A dermoscopic photograph of a skin lesion.
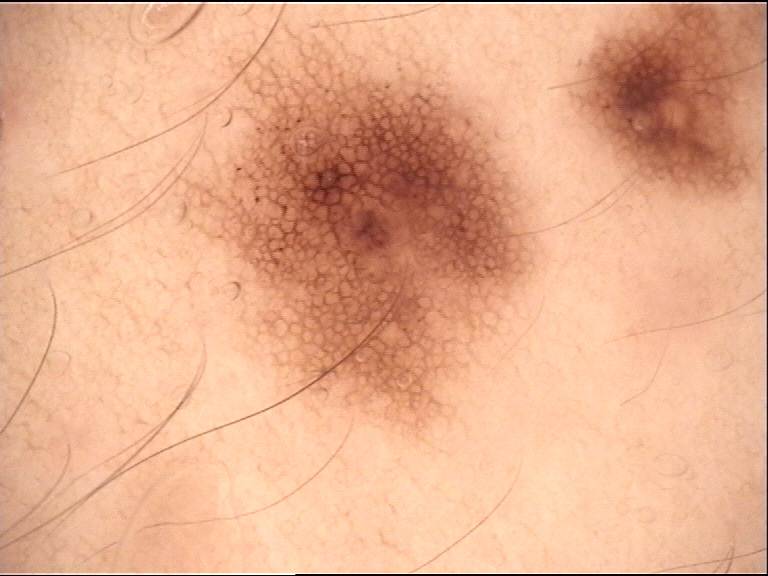Conclusion: Labeled as a benign lesion — a dysplastic junctional nevus.